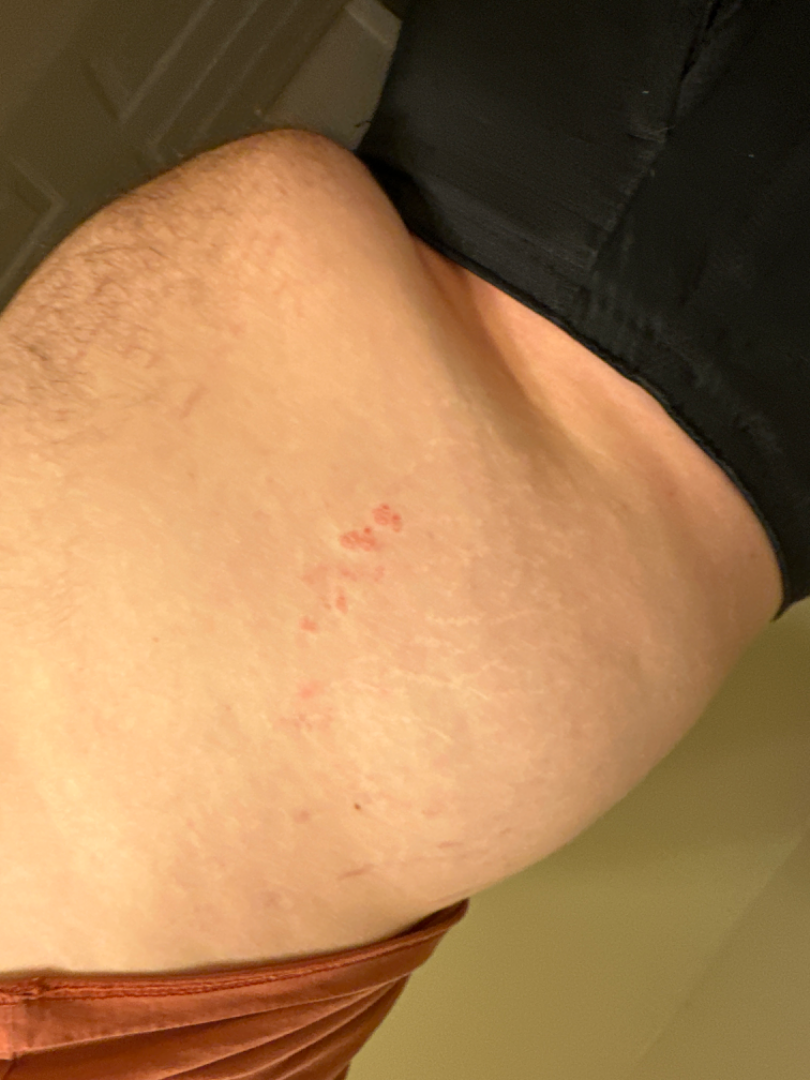Findings:
The case was indeterminate on photographic review.
Background:
An image taken at a distance. Male subject, age 18–29. The front of the torso is involved.